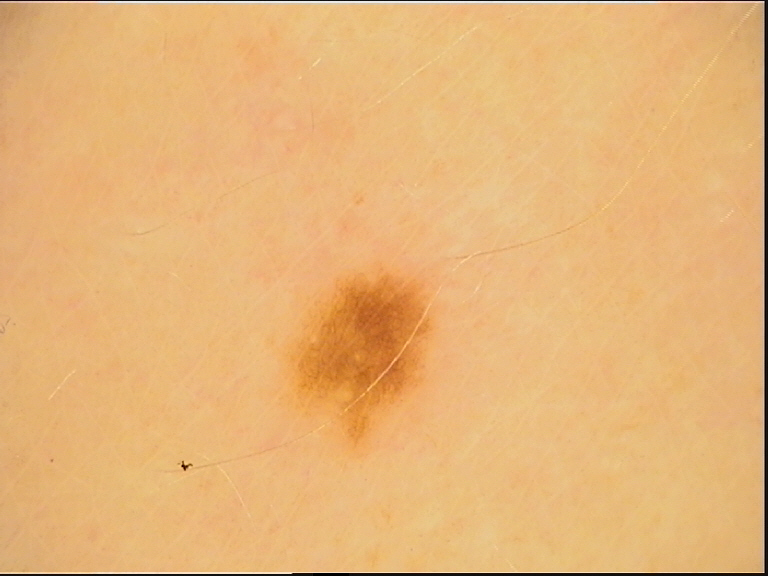Findings: A dermoscopic image of a skin lesion. Conclusion: The diagnosis was a banal lesion — a junctional nevus.